This image was taken at an angle; located on the leg:
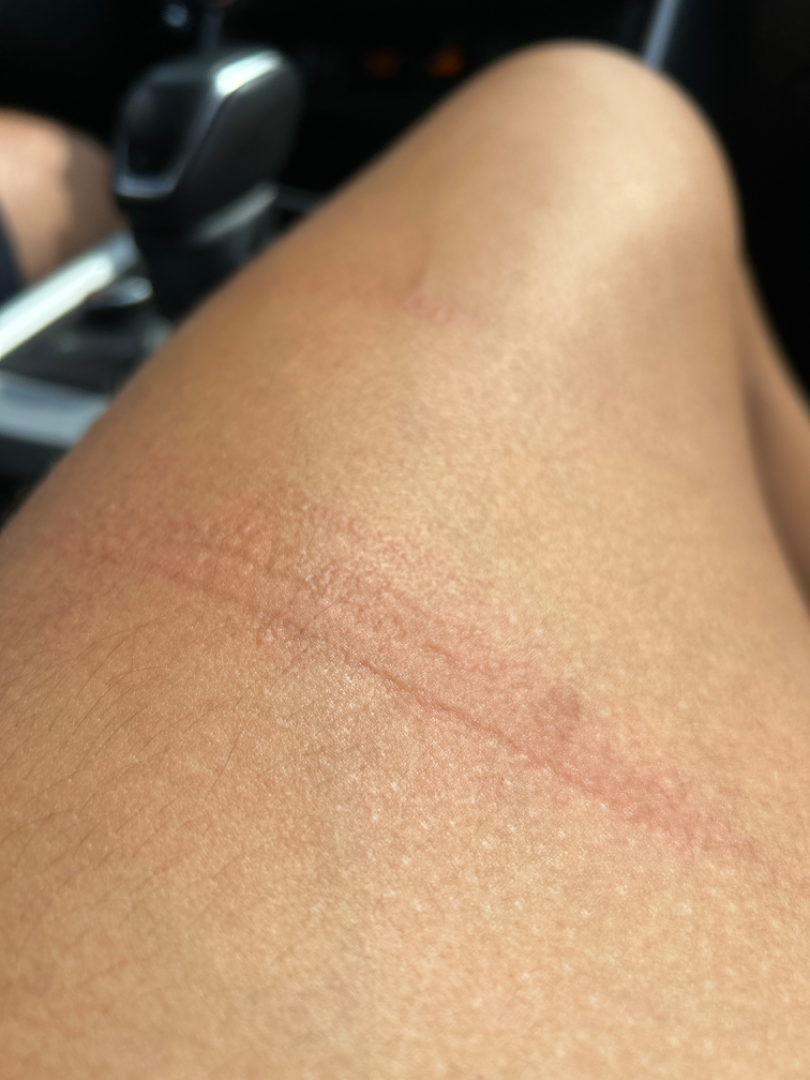<summary>
  <duration>about one day</duration>
  <differential>
    <leading>Allergic Contact Dermatitis</leading>
  </differential>
</summary>